A close-up photograph:
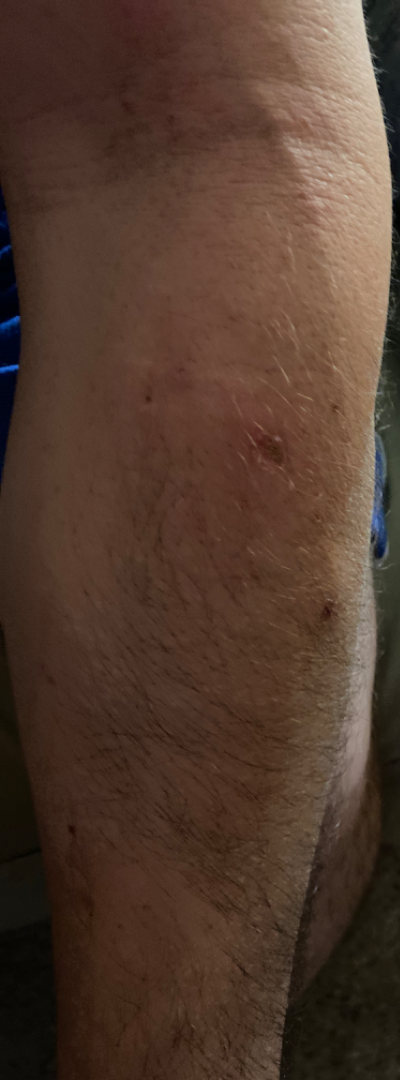Review: The reviewing dermatologist was unable to assign a differential diagnosis from the image.